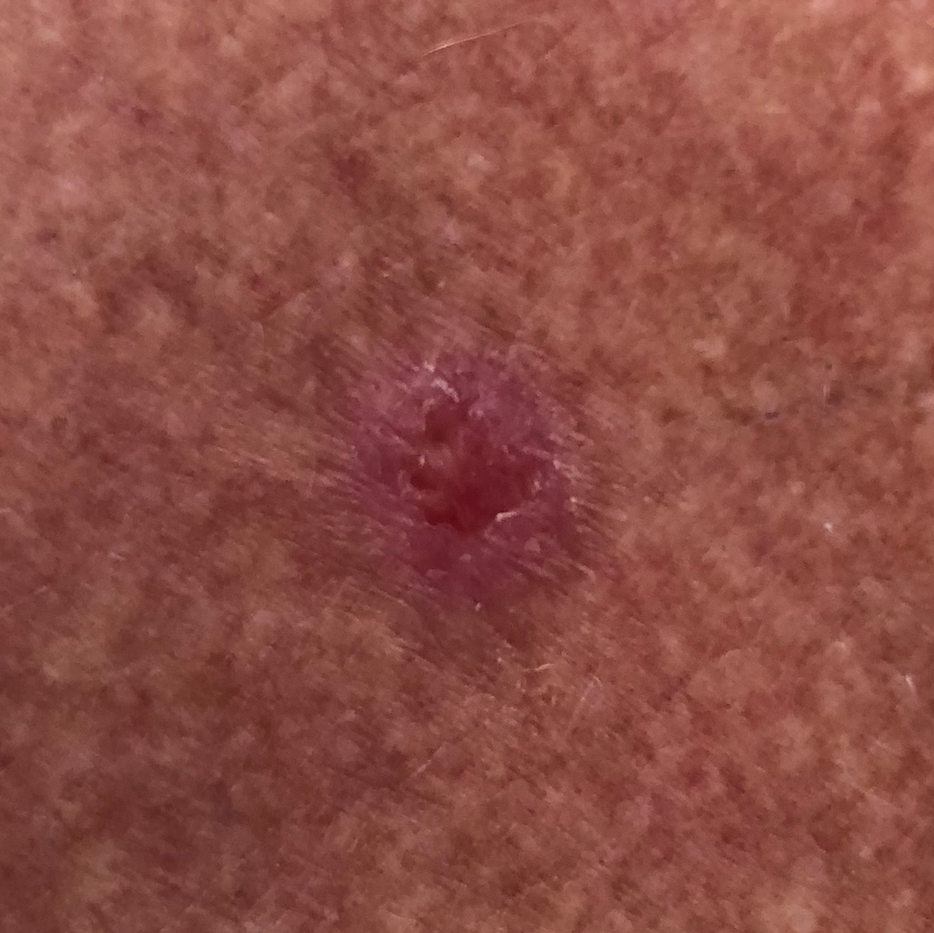Findings:
By history, pesticide exposure and prior skin cancer (patient or family). Recorded as Fitzpatrick skin type II. A smartphone photograph of a skin lesion. Located on the back. The lesion measures approximately 9 × 8 mm. By the patient's account, the lesion itches and is elevated, but has not bled and does not hurt.
Conclusion:
Confirmed on histopathology as a malignant skin lesion — a basal cell carcinoma.